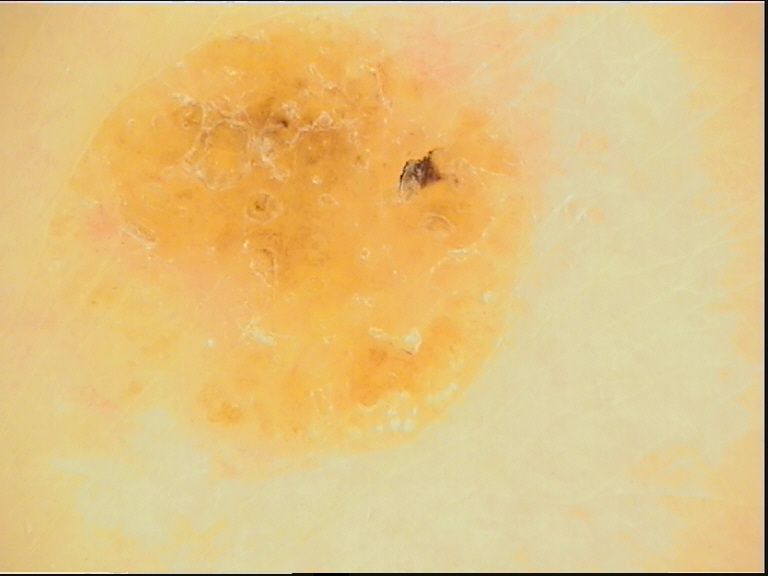A dermoscopy image of a single skin lesion.
This is a keratinocytic lesion.
Diagnosed as a seborrheic keratosis.